The lesion involves the arm and leg; the photo was captured at a distance — 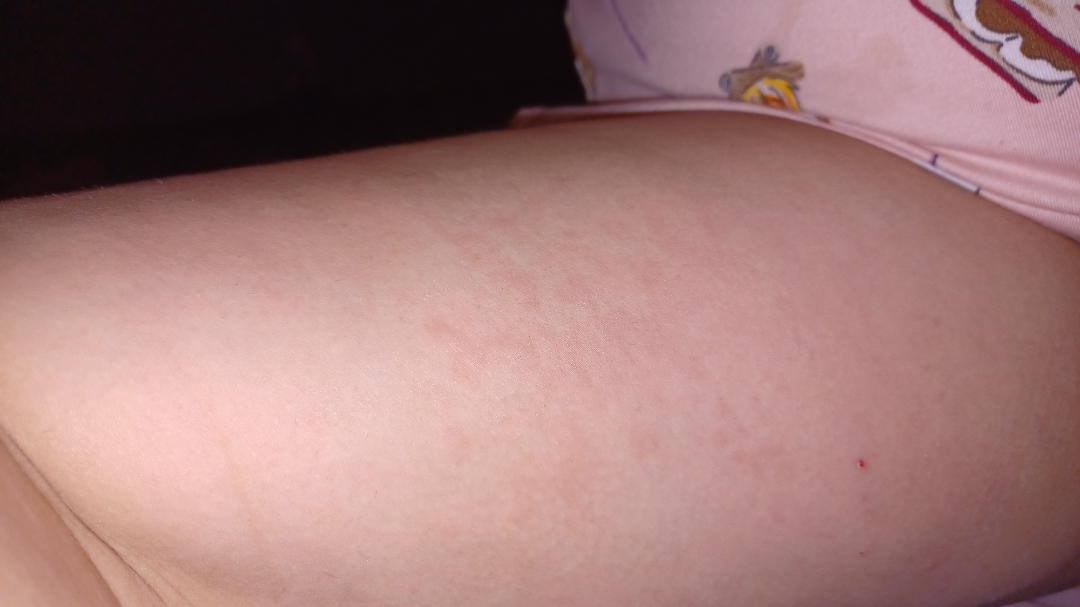Q: Could the case be diagnosed?
A: unable to determine
Q: How long has this been present?
A: less than one week
Q: How does the lesion feel?
A: raised or bumpy
Q: What symptoms does the patient report?
A: enlargement and itching
Q: Patient's own categorization?
A: a rash